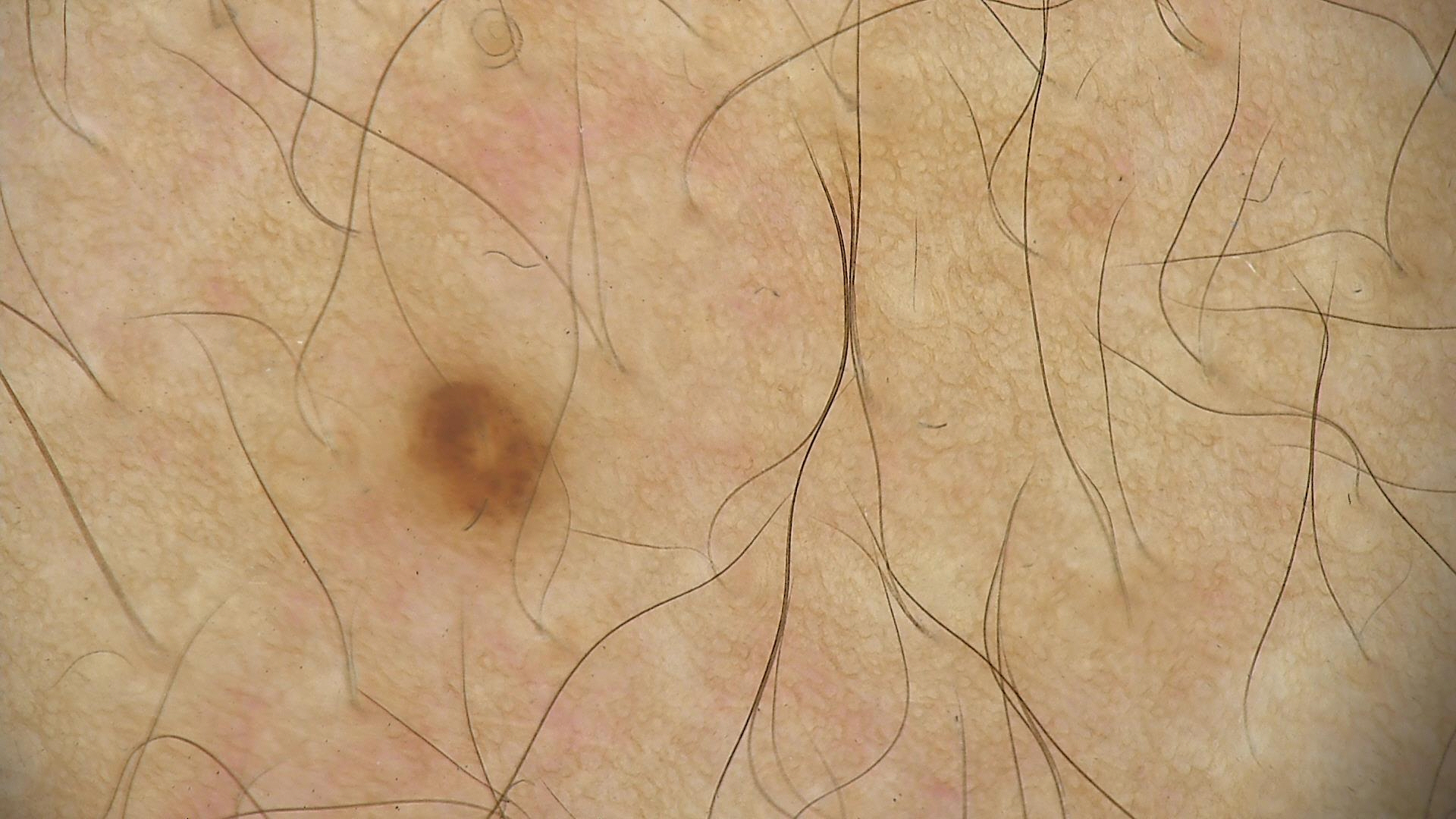assessment: dysplastic junctional nevus (expert consensus)